A male patient 69 years of age; history notes prior malignancy (patient or family); a clinical close-up photograph of a skin lesion; recorded as FST II: 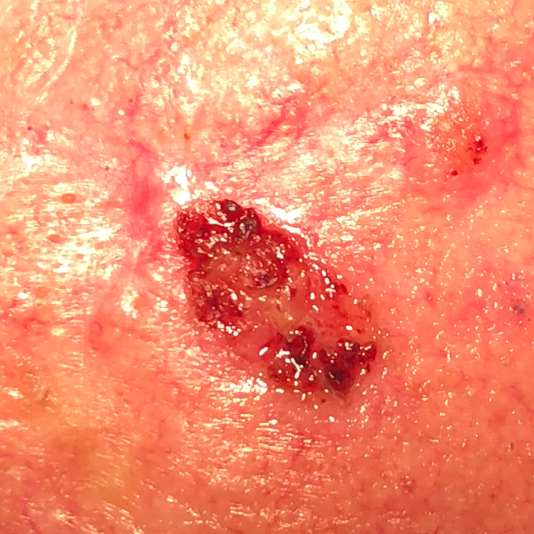anatomic site = the face
diameter = 10x4 mm
symptoms = itching, pain, elevation, growth, bleeding
pathology = basal cell carcinoma (biopsy-proven)